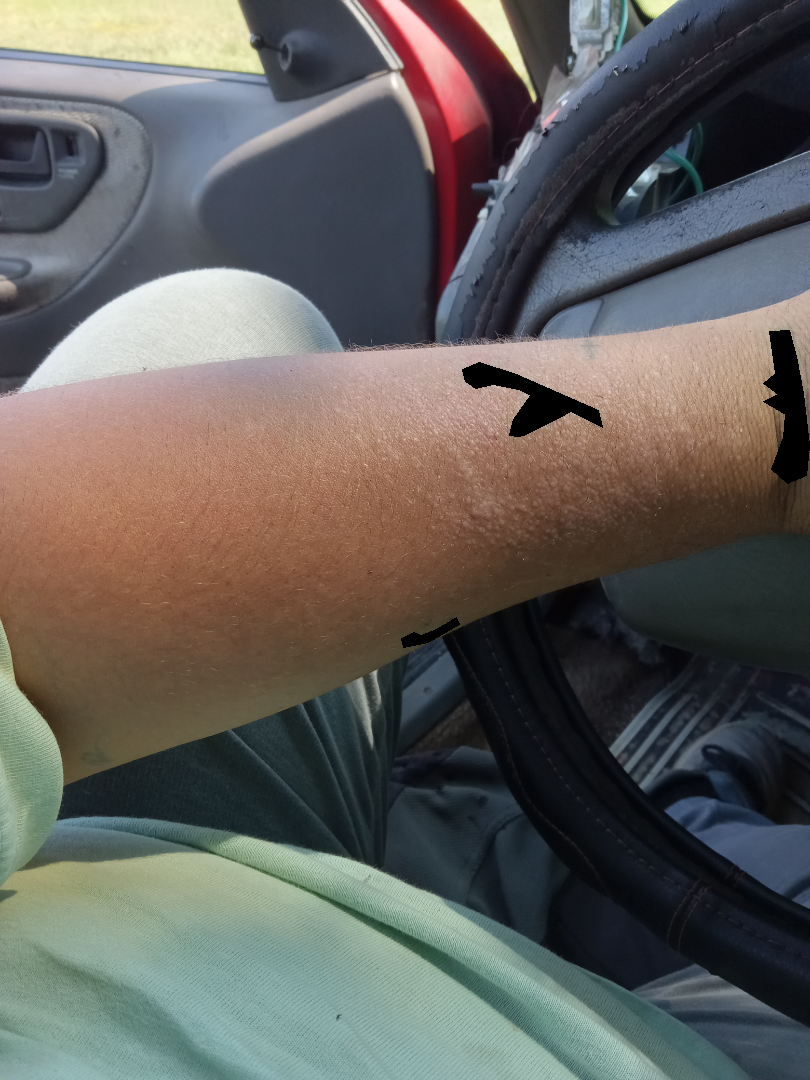Background: Present for three to twelve months. Located on the arm. An image taken at a distance. The contributor notes pain and itching. The contributor notes the lesion is raised or bumpy and fluid-filled. Findings: Lichen planus/lichenoid eruption (leading).